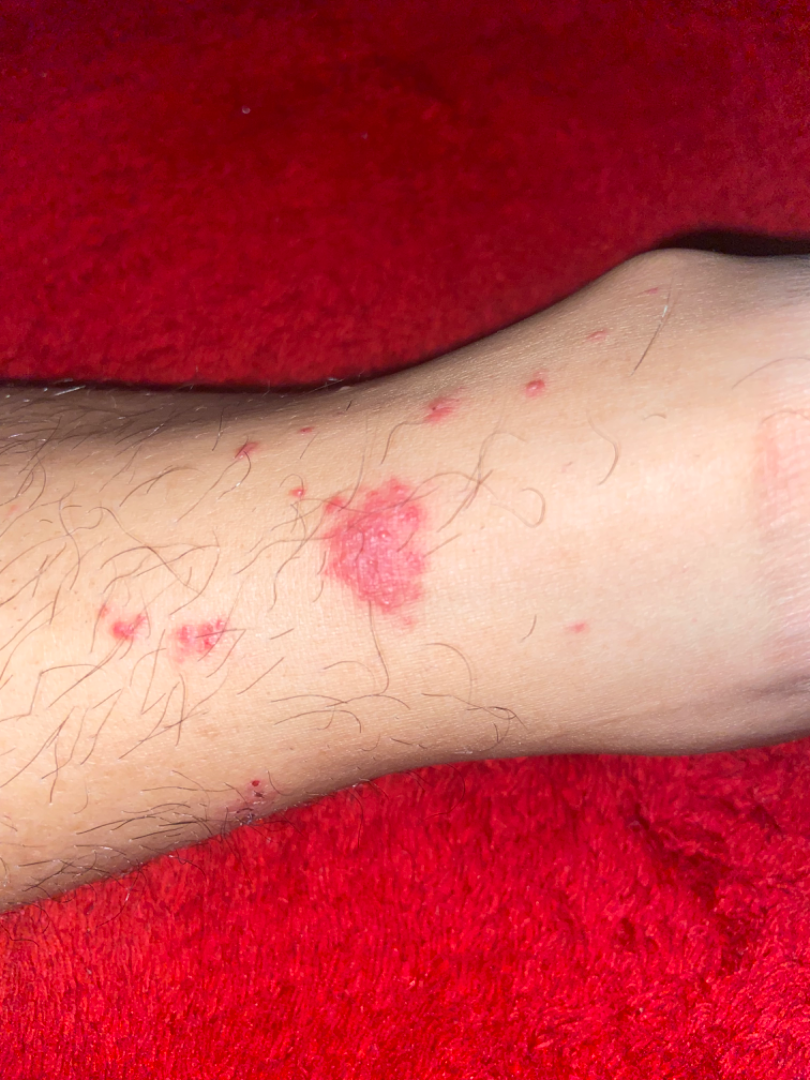assessment: indeterminate from the photograph.